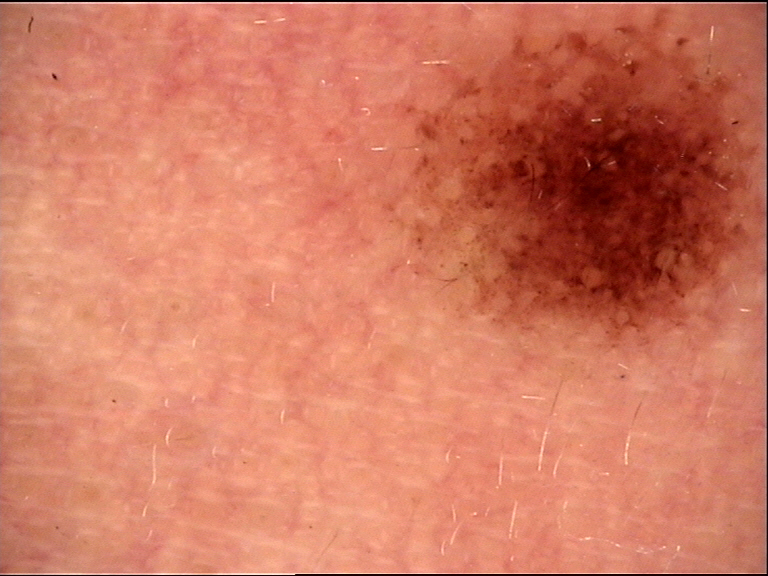Classified as a Miescher nevus.